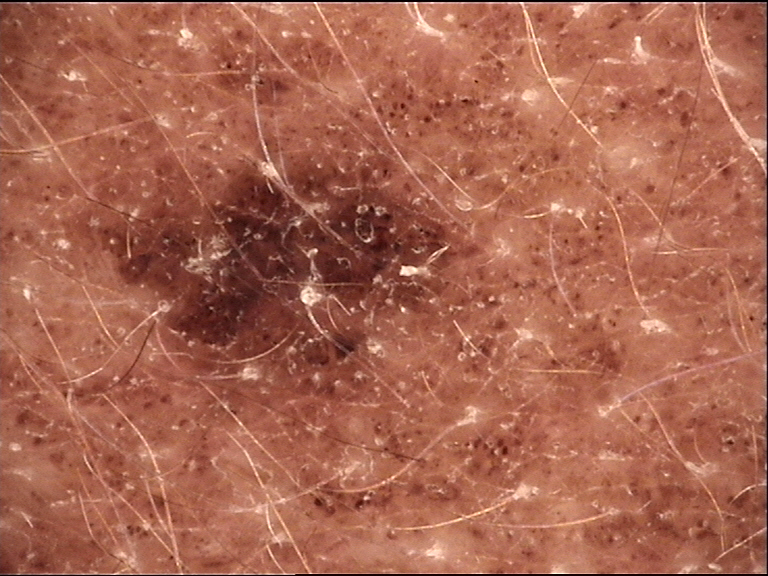A dermatoscopic image of a skin lesion.
The architecture is that of a banal lesion.
The diagnostic label was a congenital compound nevus.